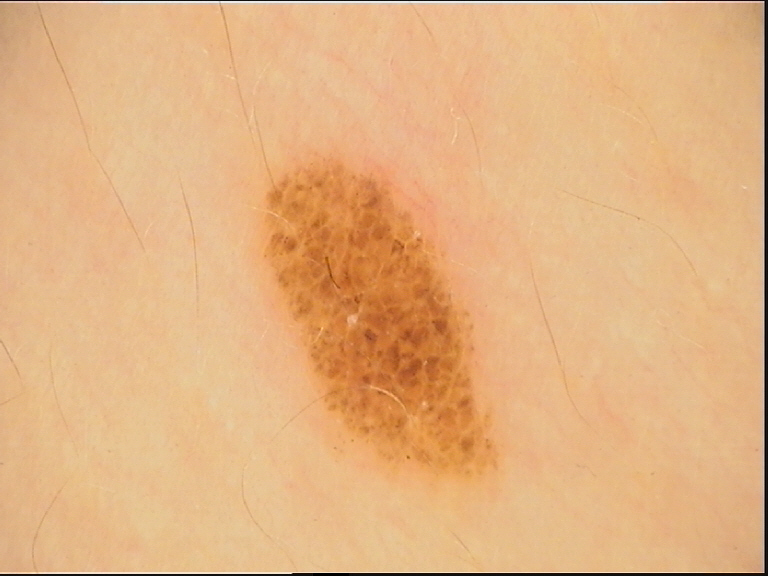Classified as a dysplastic compound nevus.